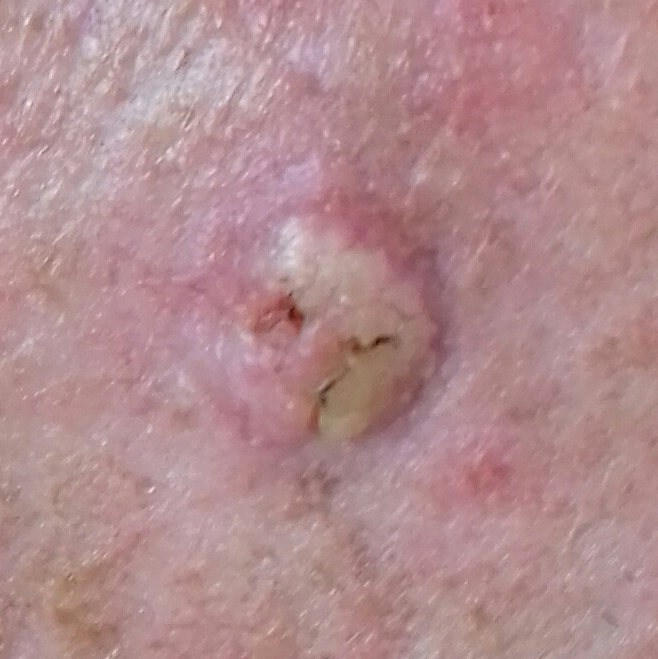subject: male, 73 years of age
image: smartphone clinical photo
location: the face
symptoms: itching, elevation
diagnostic label: squamous cell carcinoma (biopsy-proven)